A dermoscopic photograph of a skin lesion. Recorded as Fitzpatrick phototype II — 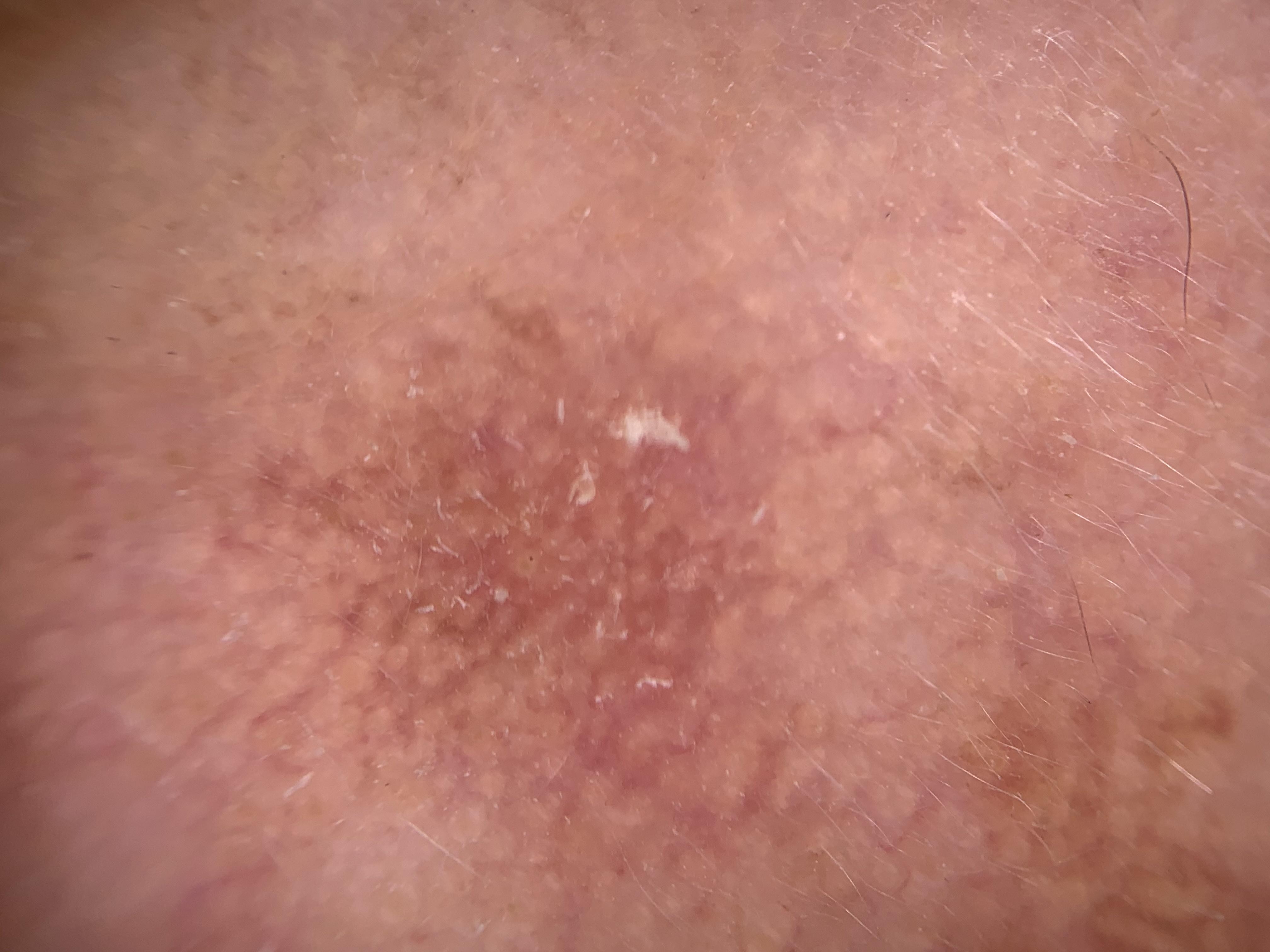{
  "lesion_location": {
    "region": "the head or neck"
  },
  "diagnosis": {
    "name": "Solar or actinic keratosis",
    "malignancy": "indeterminate",
    "confirmation": "expert clinical impression",
    "lineage": "epidermal"
  }
}